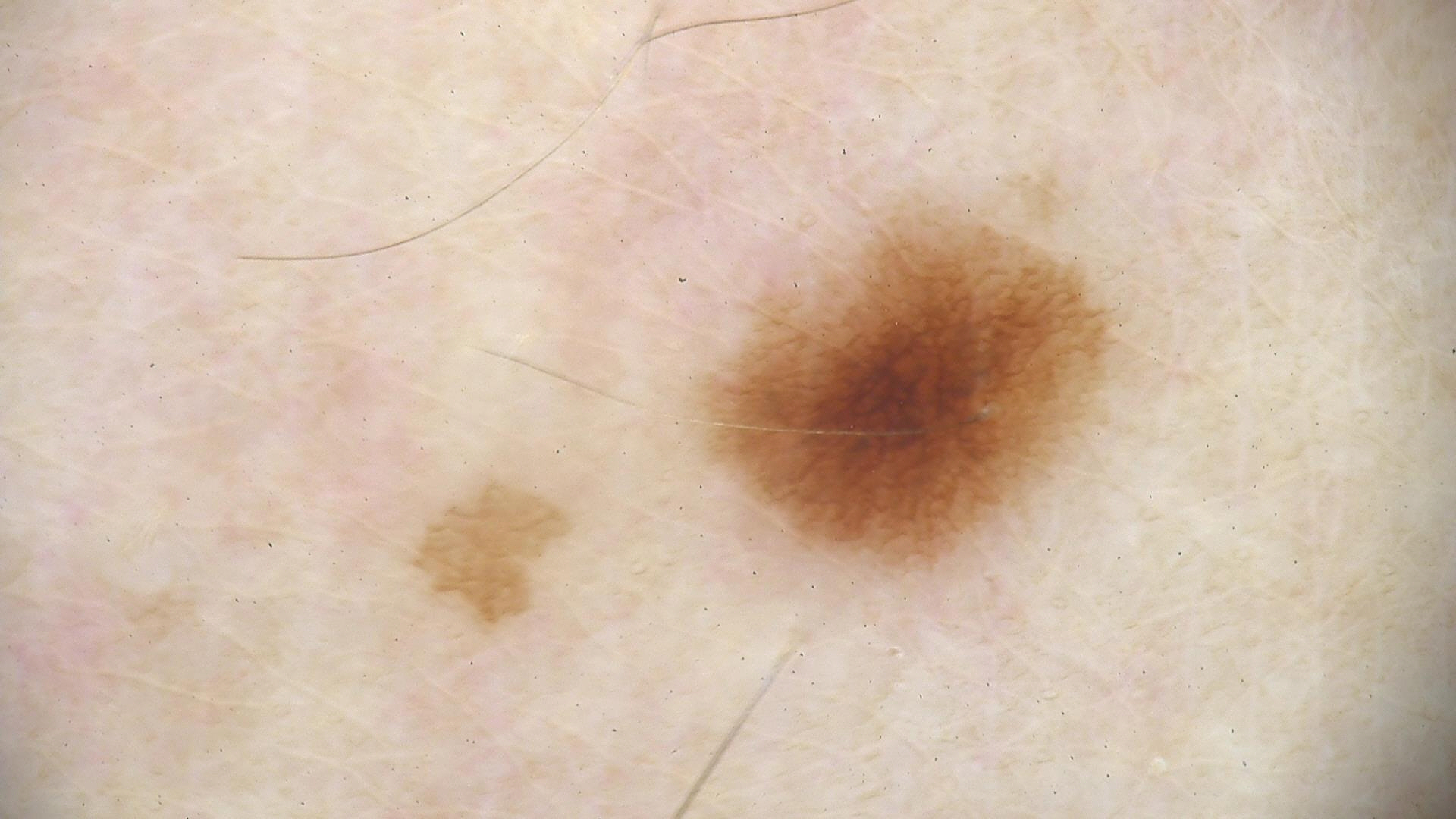Findings: Dermoscopy of a skin lesion. Conclusion: Classified as a benign lesion — a dysplastic junctional nevus.